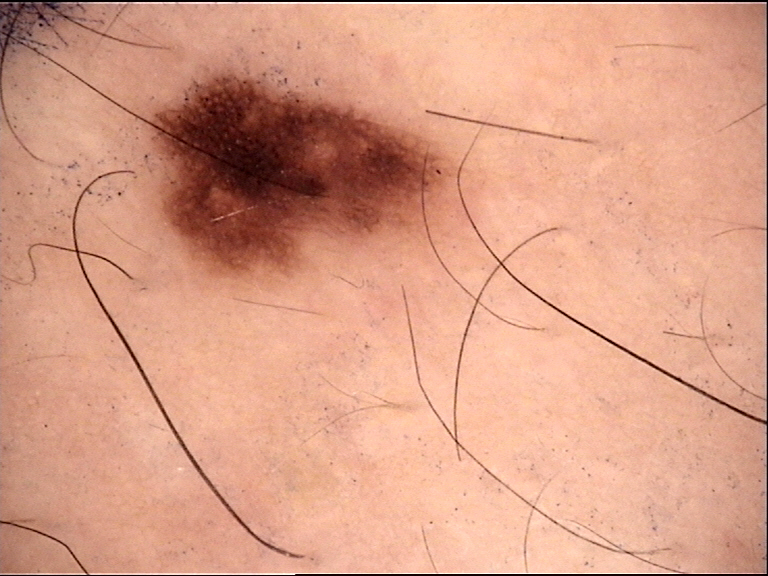* image type · dermatoscopy
* diagnostic label · dysplastic junctional nevus (expert consensus)